A dermoscopic photograph of a skin lesion.
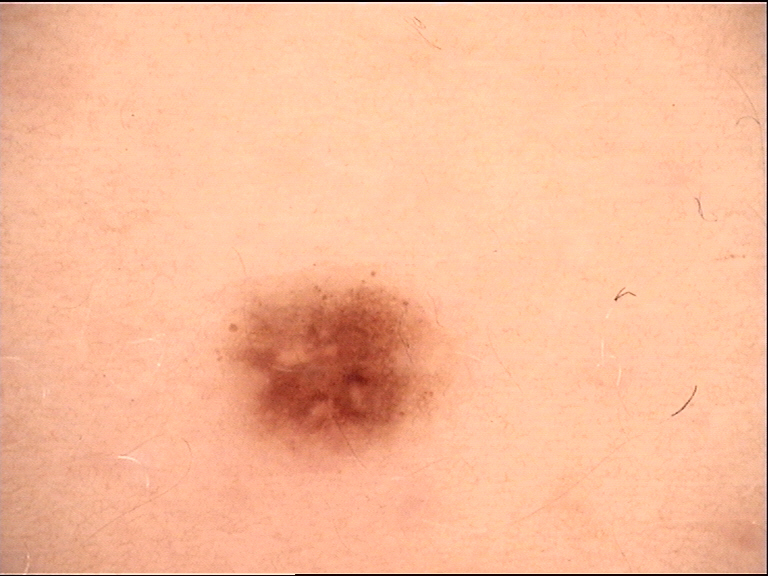Impression:
Classified as a dysplastic junctional nevus.